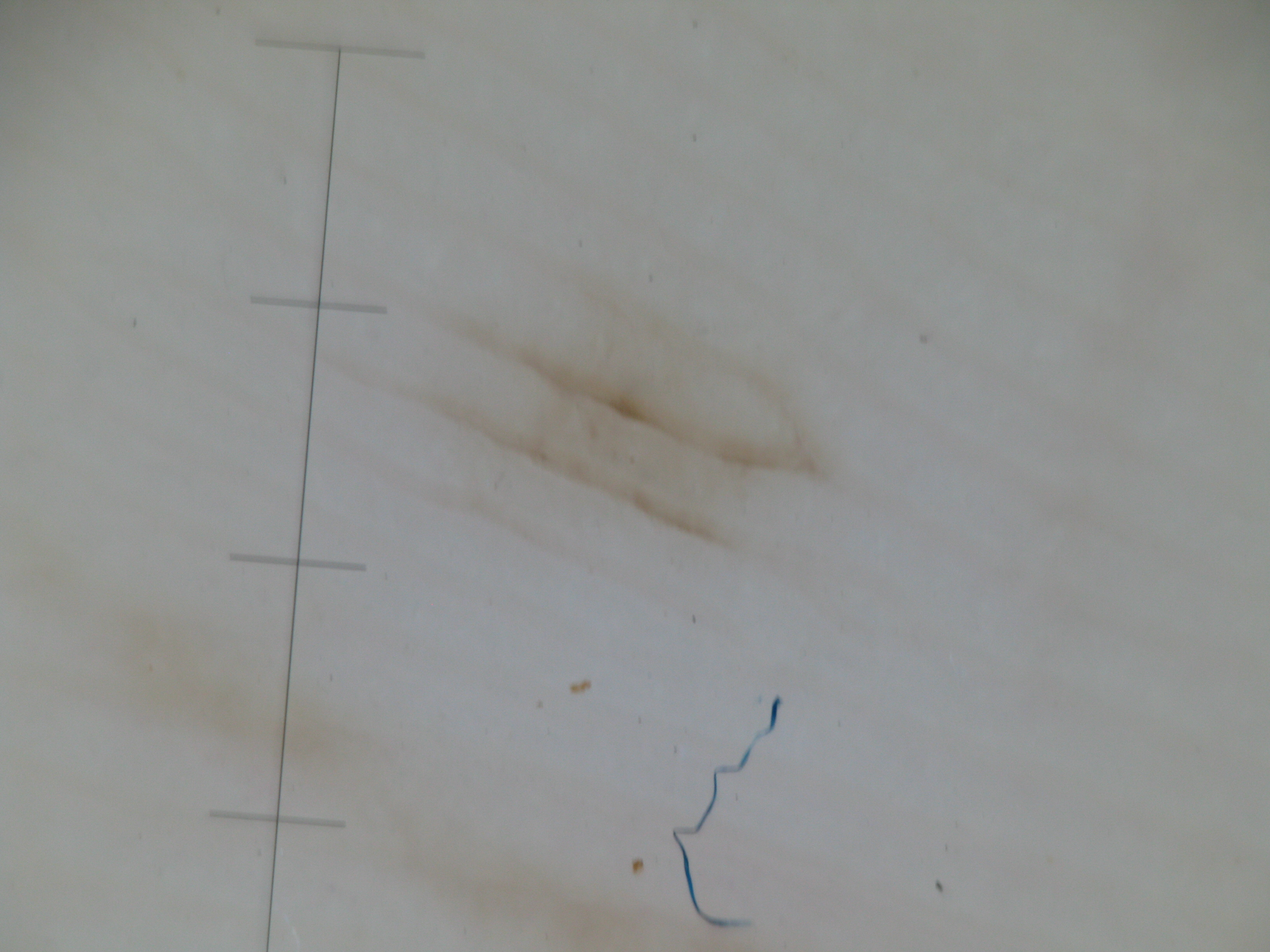modality: dermoscopy | class: acral junctional nevus (expert consensus).